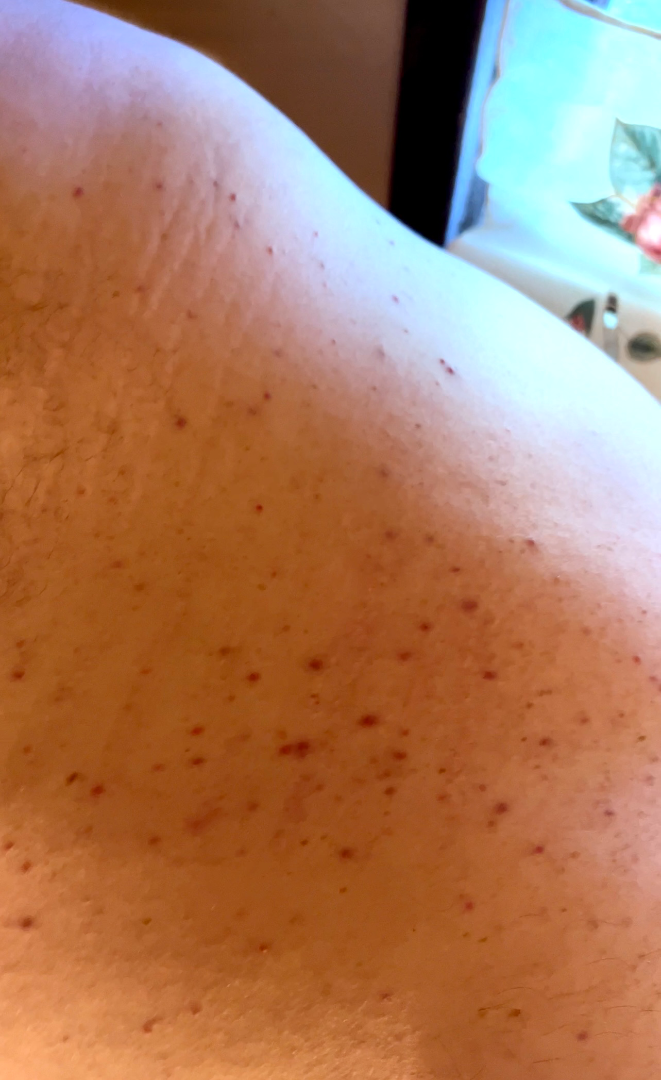Background: The photo was captured at an angle. The subject is 40–49, male. The contributor reports the condition has been present for less than one week. The lesion is described as flat and raised or bumpy. Symptoms reported: bothersome appearance. The back of the torso is involved. The contributor reports associated joint pain. The patient described the issue as a rash. Findings: A single dermatologist reviewed the case: most consistent with Leukocytoclastic Vasculitis; also raised was Pityriasis lichenoides; also on the differential is Folliculitis.